A dermoscopic photograph of a skin lesion: 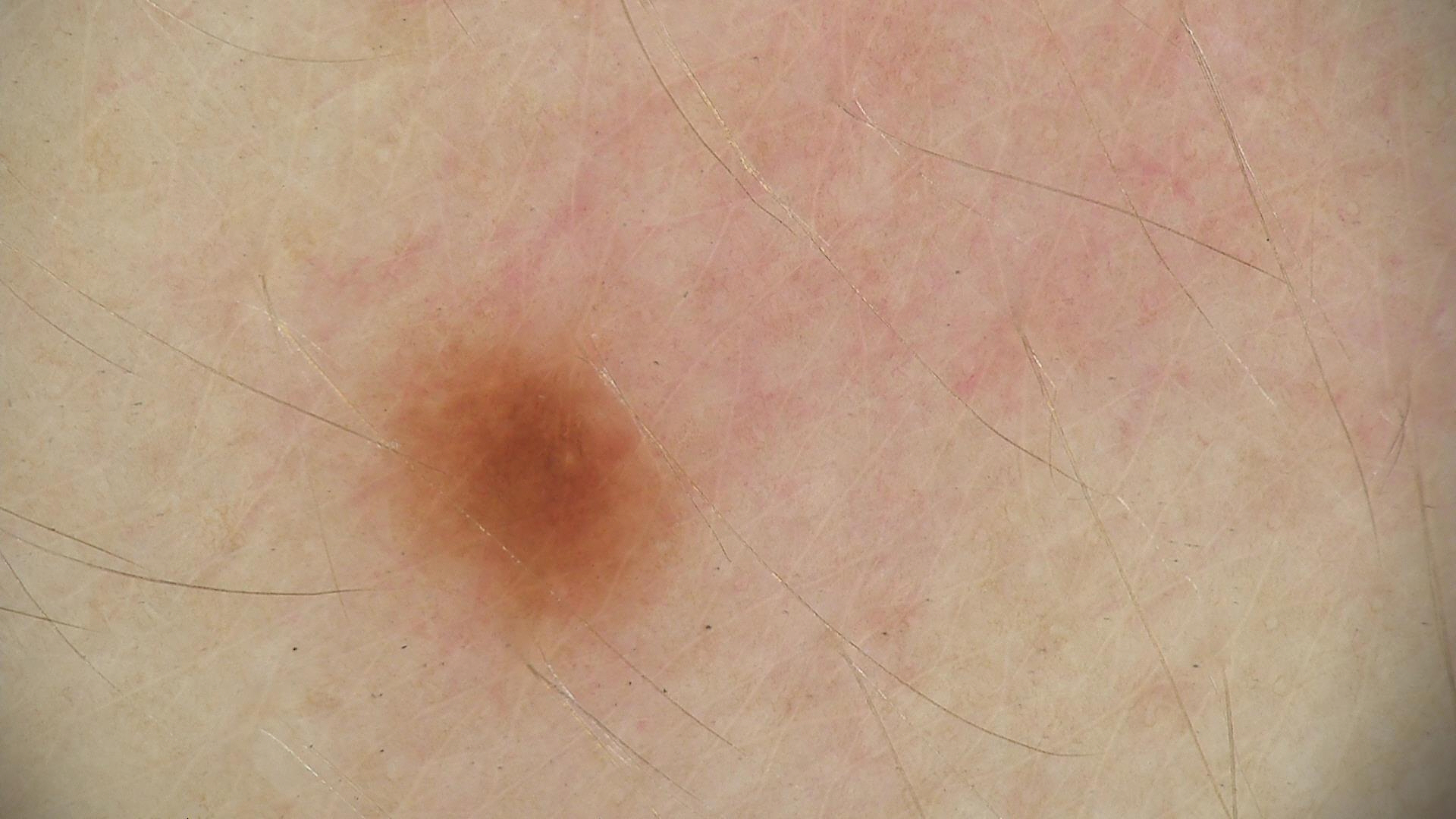The morphology is that of a banal lesion. Consistent with a junctional nevus.